Self-categorized by the patient as a rash; the photograph is a close-up of the affected area; the patient notes burning, pain and itching; the lesion involves the leg; the lesion is described as raised or bumpy — 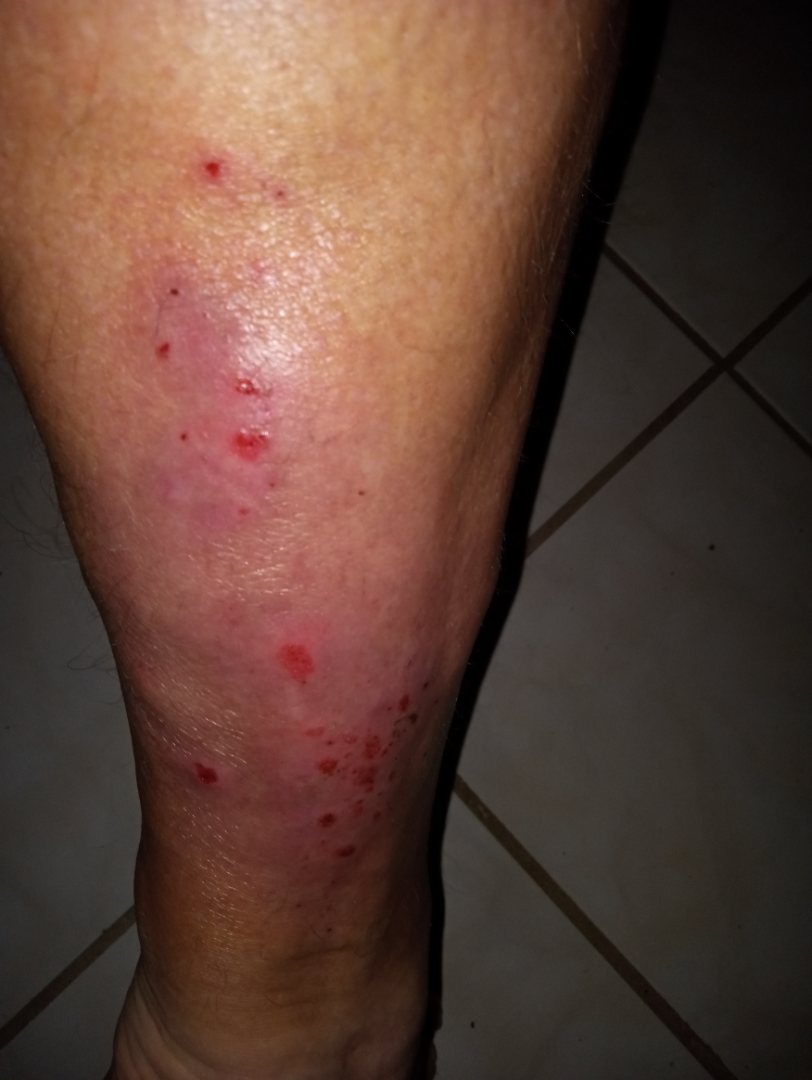Review: On dermatologist assessment of the image, Eczema (considered); Cutaneous T Cell Lymphoma (considered); Lichen Simplex Chronicus (considered).